A dermoscopic image of a skin lesion: 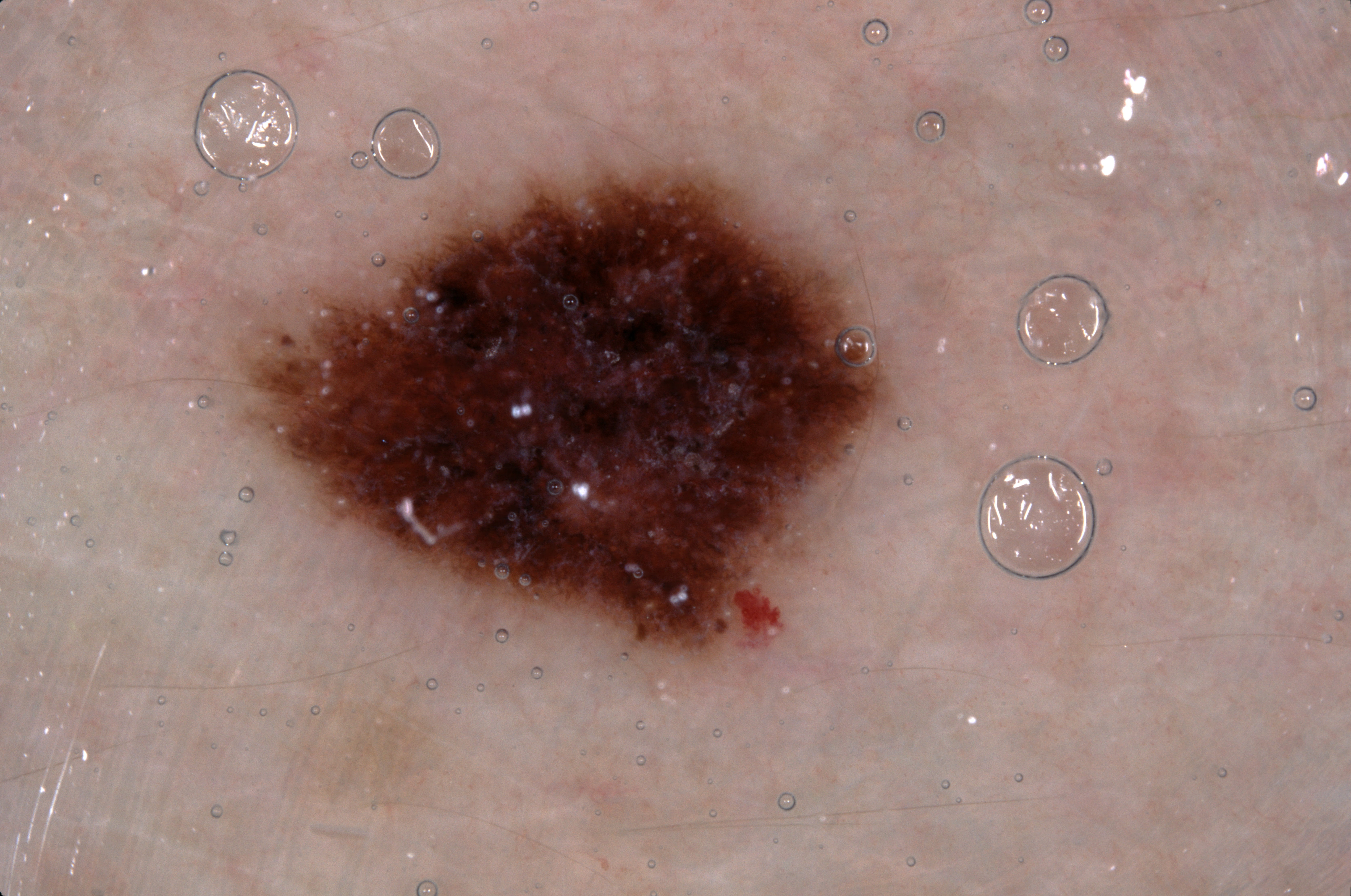bounding box — 229 155 897 667
dermoscopic features — pigment network and milia-like cysts; absent: negative network and streaks
extent — ~18% of the field
assessment — a melanocytic nevus, a benign skin lesion